The contributor is 50–59, female · close-up view · the affected area is the front of the torso: 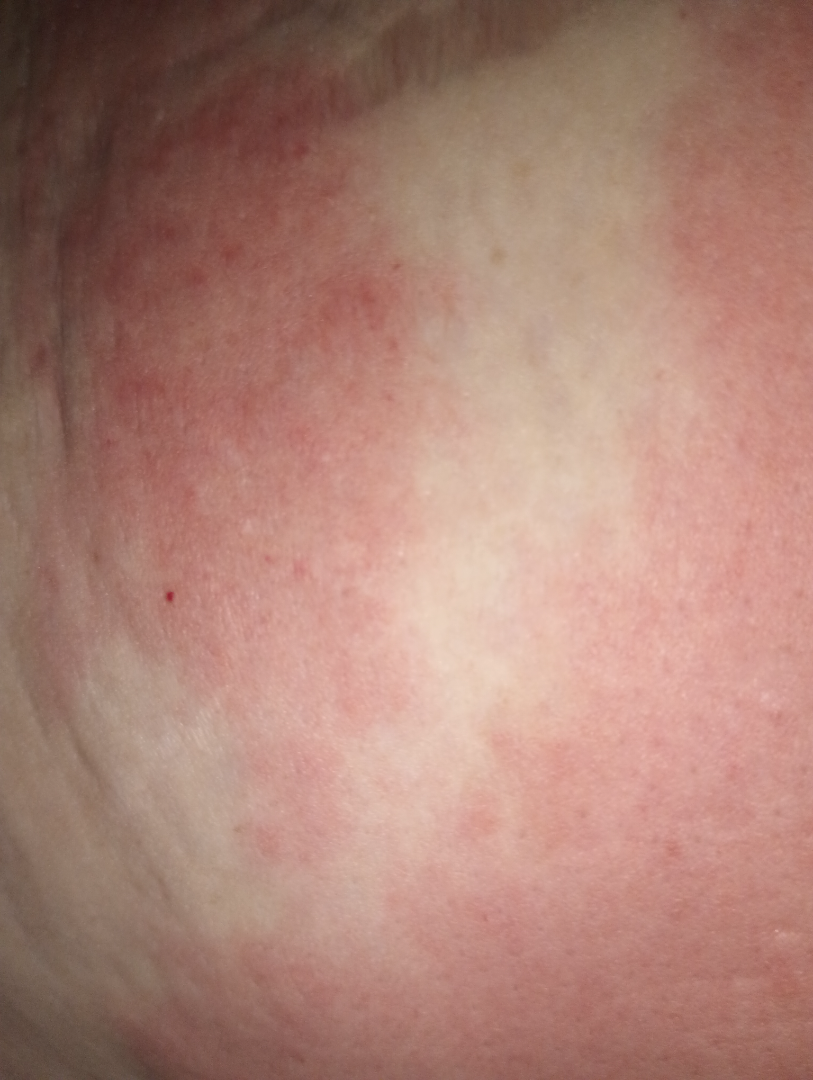– constitutional symptoms · fever, joint pain and fatigue
– present for · less than one week
– reported symptoms · none reported
– described texture · raised or bumpy
– assessment · the differential includes Contact dermatitis and Urticaria, with no clear leading consideration